A skin lesion imaged with a dermatoscope.
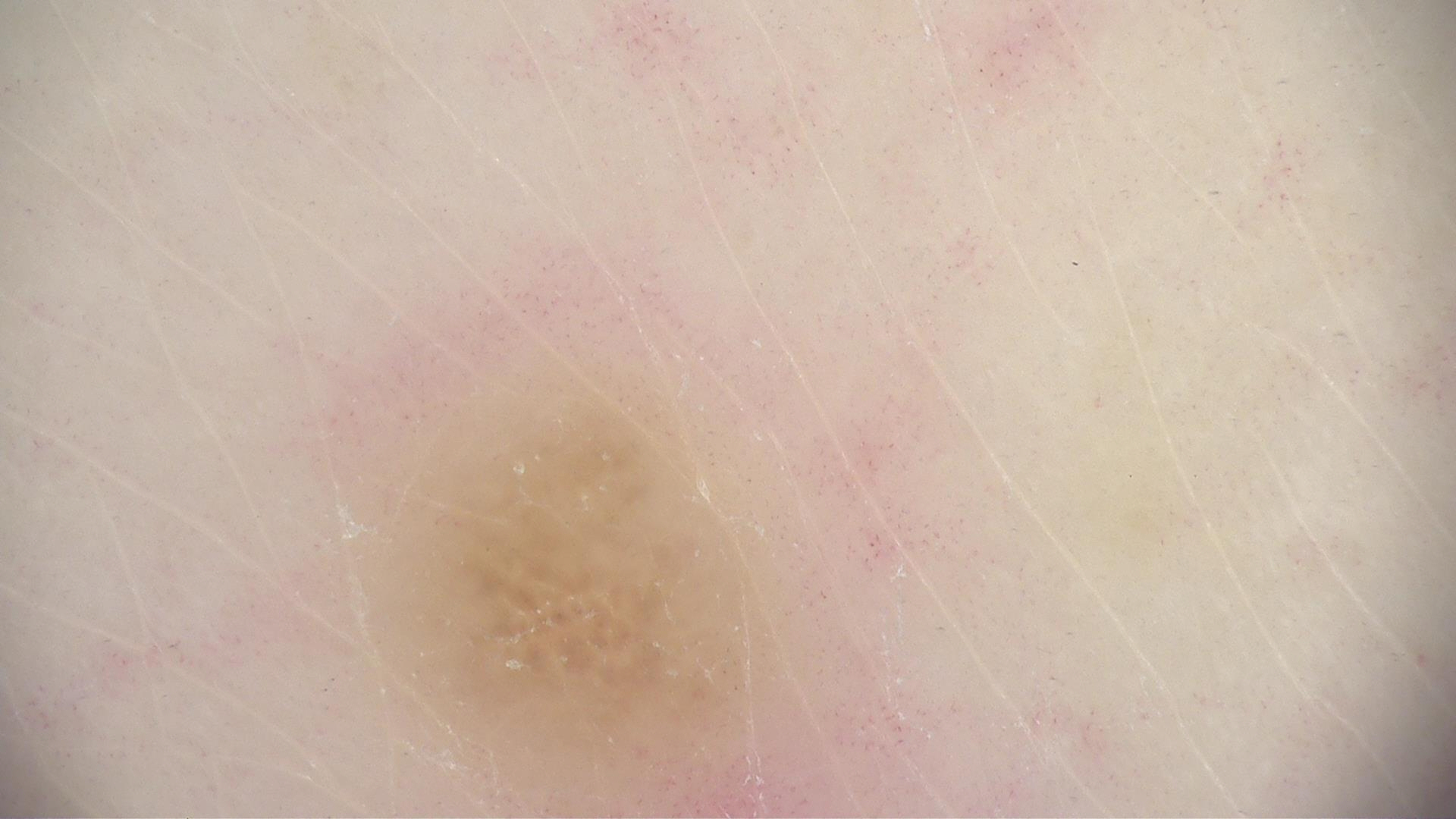Labeled as a banal lesion — a dermal nevus.